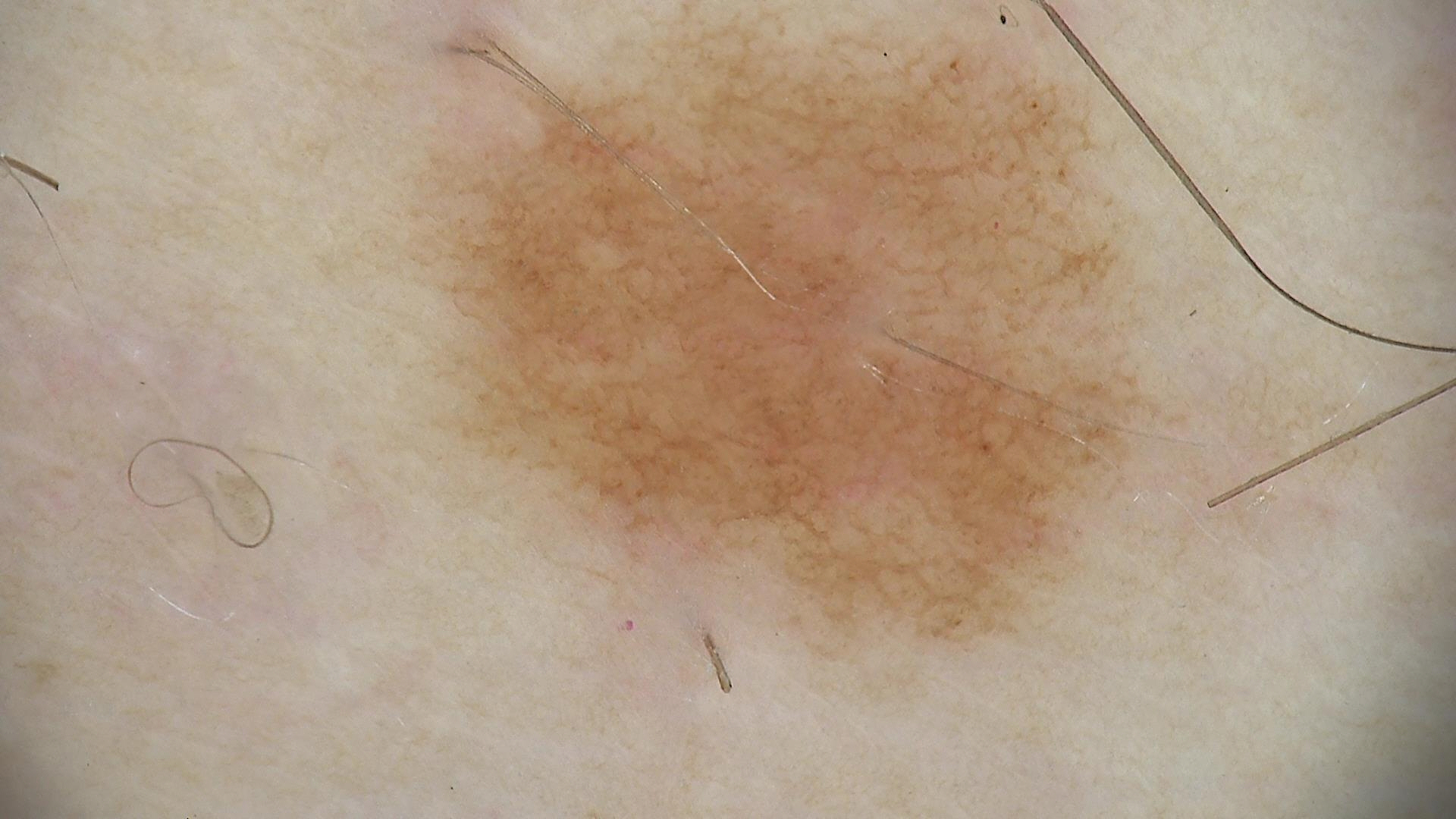• class: dysplastic junctional nevus (expert consensus)